This is a close-up image; the arm is involved — 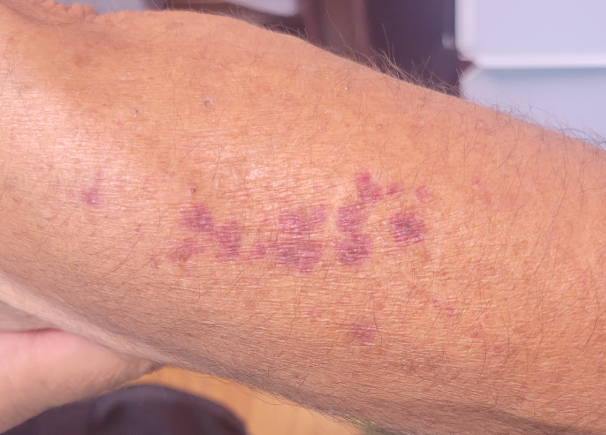texture = flat, assessment = the impression on review was ecchymoses.